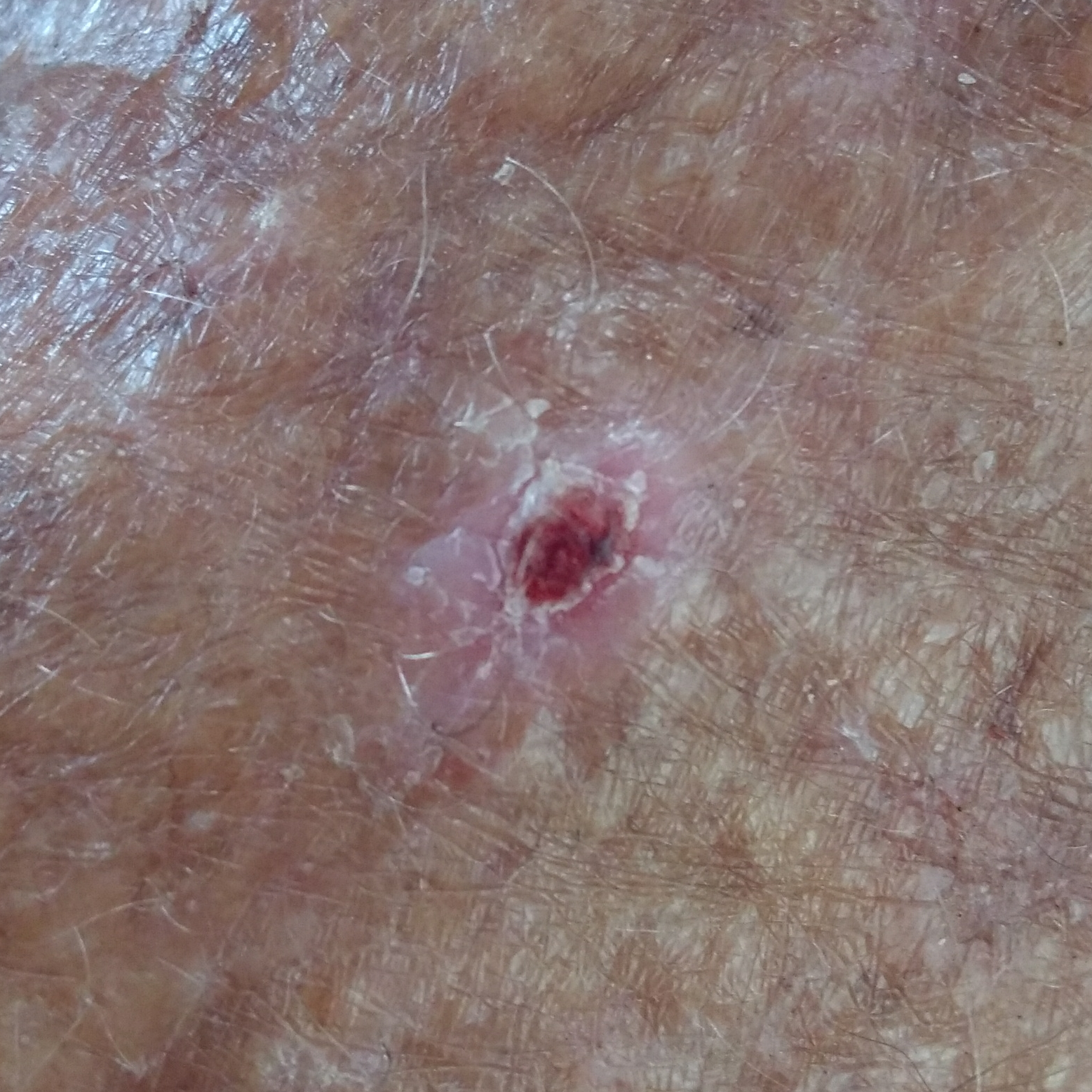pathology — actinic keratosis (biopsy-proven)